The patient says their skin reddens with sun exposure · a female subject 73 years old · collected as part of a research study, without a referral diagnosis — 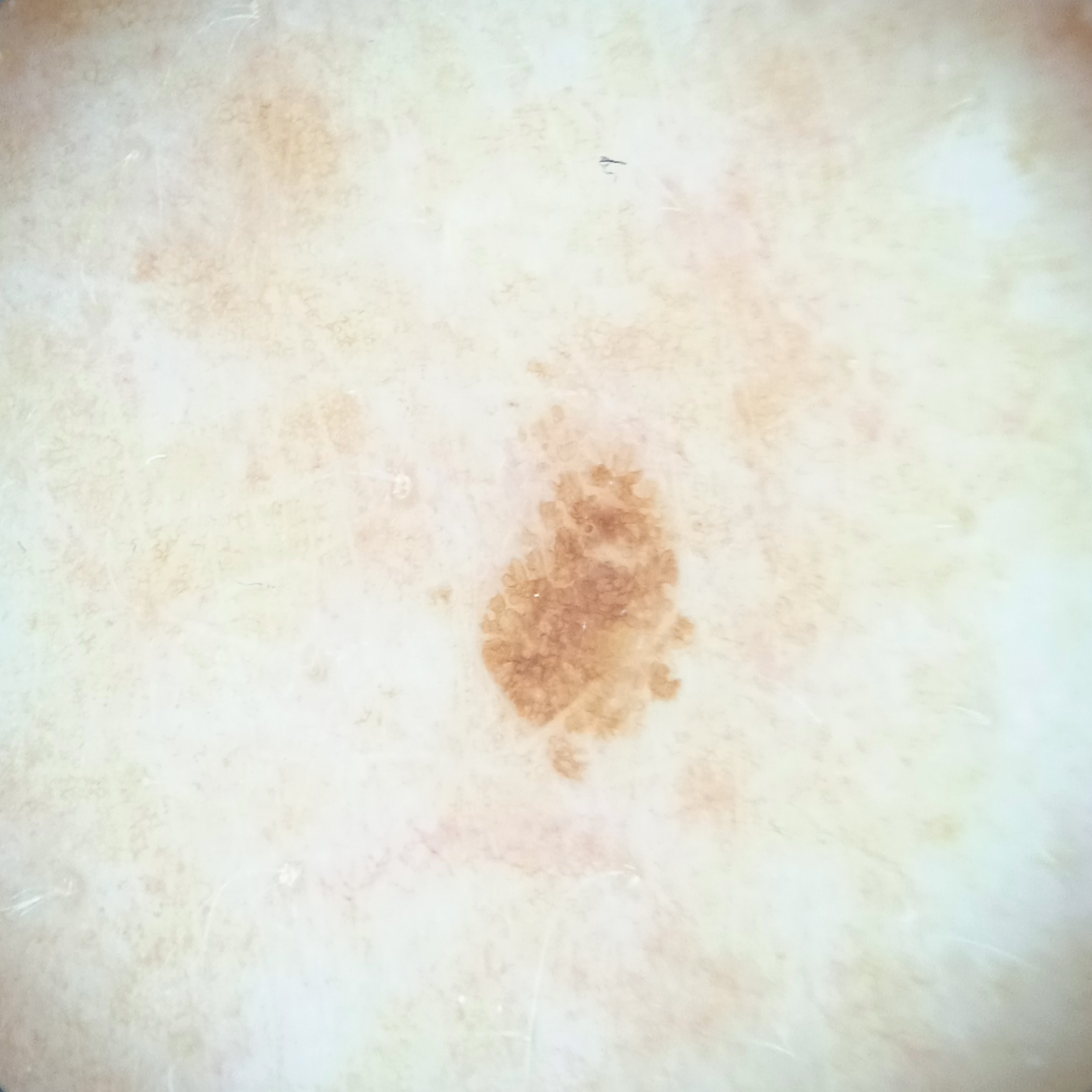lesion_location: the back
lesion_size:
  diameter_mm: 3.9
diagnosis:
  name: seborrheic keratosis
  malignancy: benign